A dermoscopic photograph of a skin lesion: 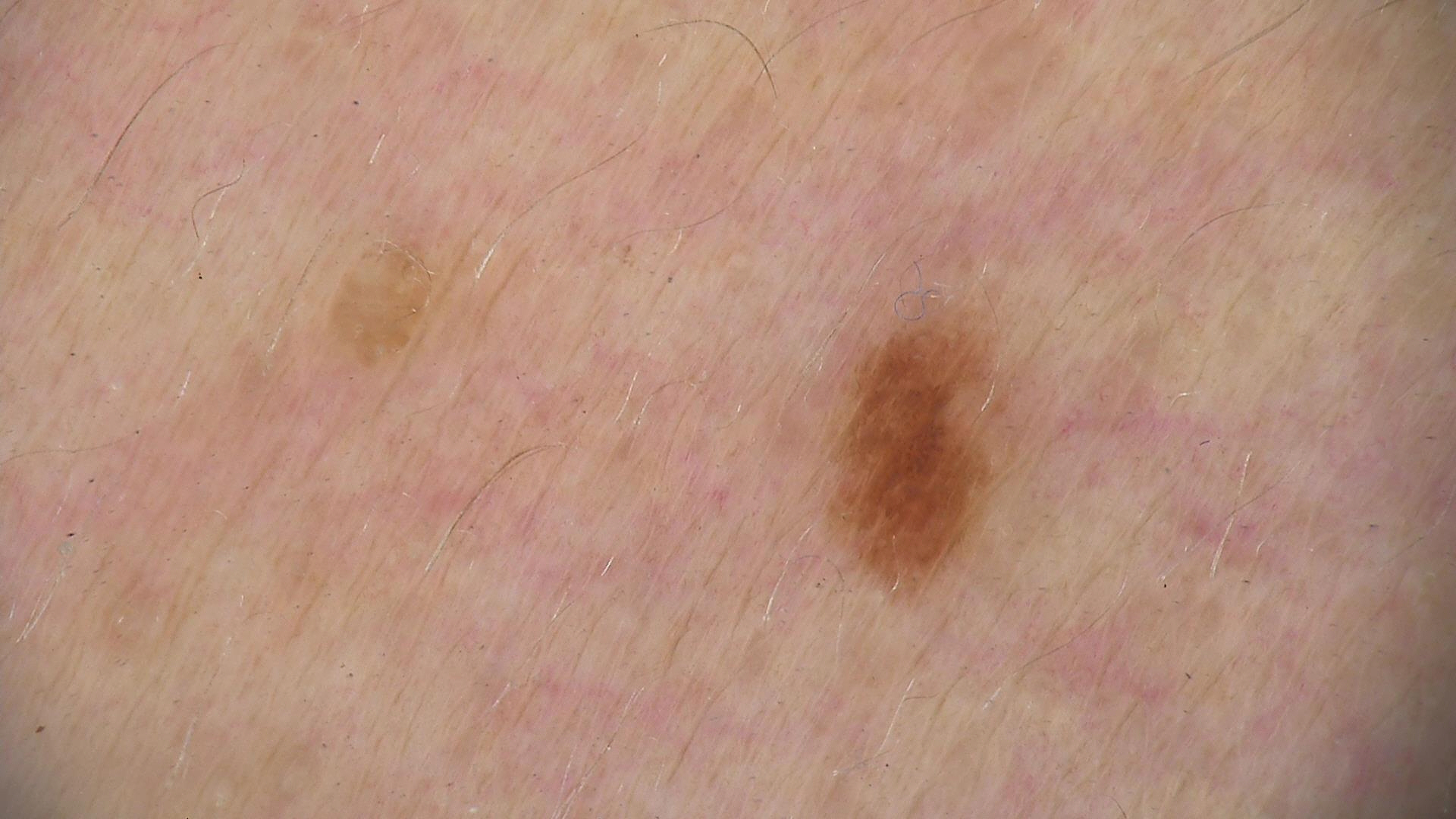Impression: The diagnosis was a benign lesion — a dysplastic junctional nevus.